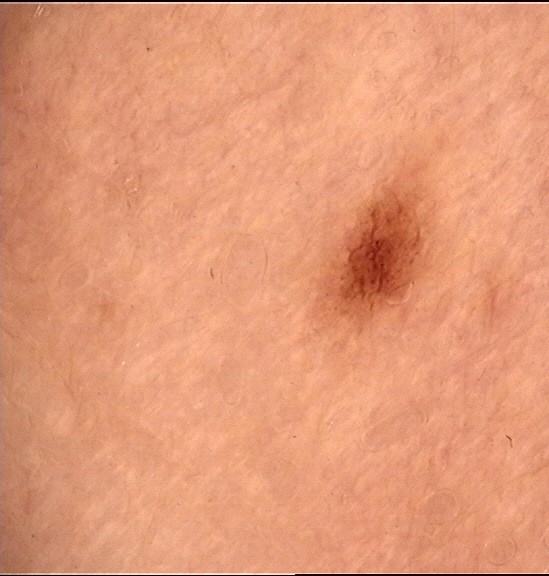Q: What was the diagnostic impression?
A: dysplastic junctional nevus (expert consensus)